Female subject, age 18–29. The photo was captured at an angle. The affected area is the head or neck: 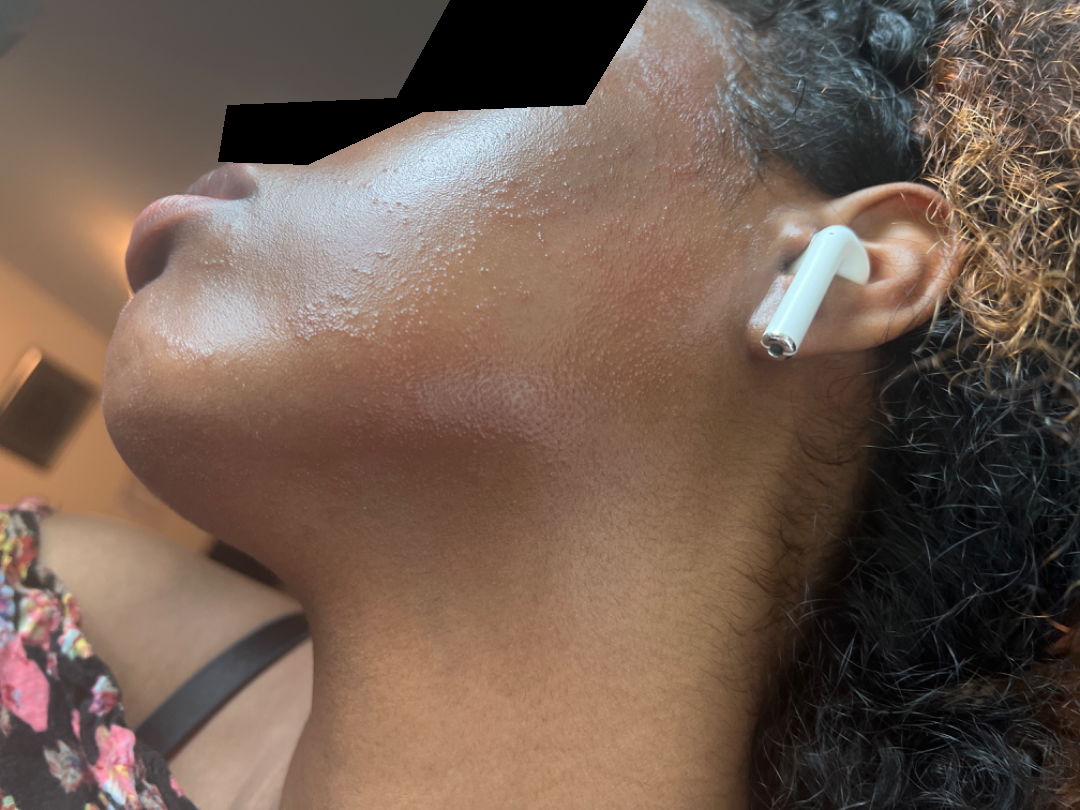<summary>
  <differential>
    <tied_lead>Contact dermatitis, Allergic Contact Dermatitis</tied_lead>
    <unlikely>Acne, Miliaria</unlikely>
  </differential>
</summary>